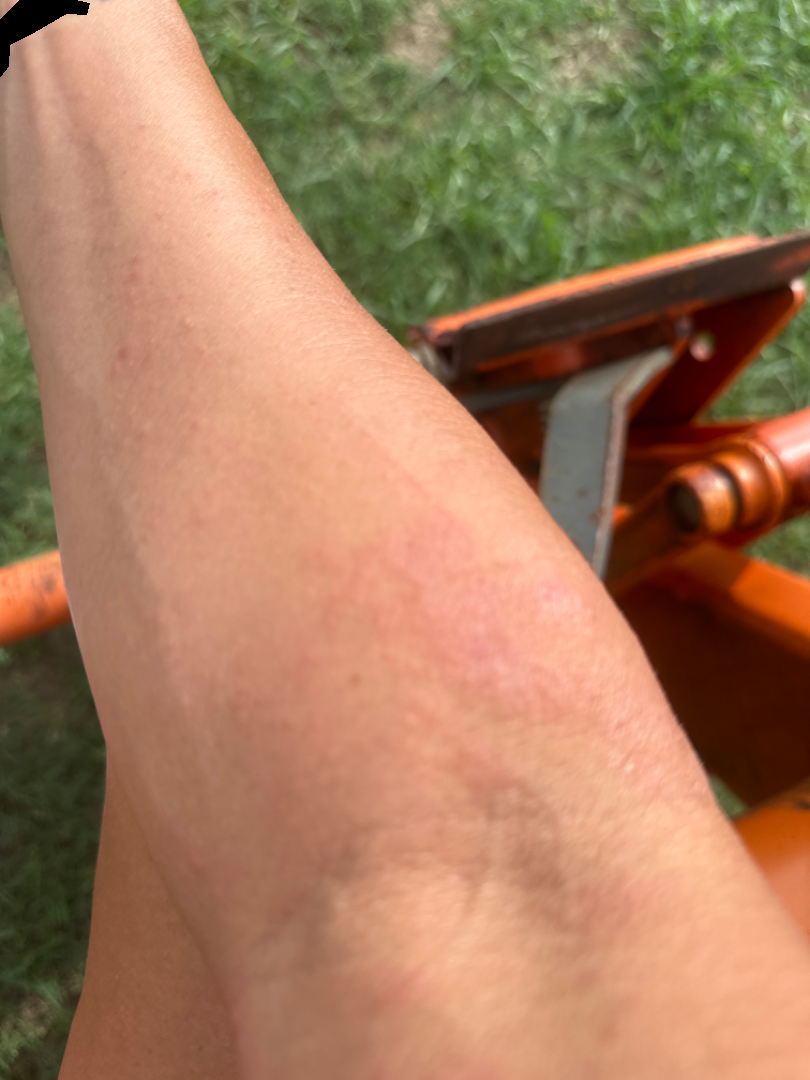Clinical context: The lesion involves the arm. This is a close-up image. Assessment: Eczema (leading); Allergic Contact Dermatitis (possible).